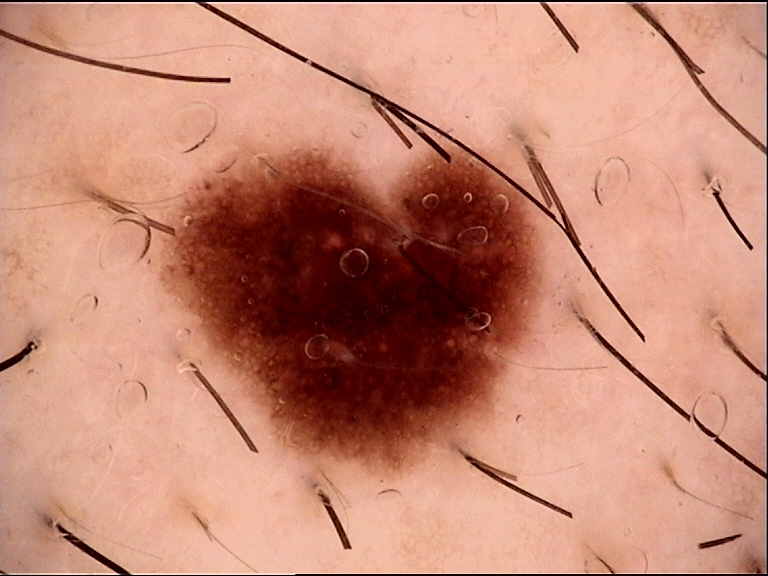Q: What is the diagnosis?
A: dysplastic junctional nevus (expert consensus)